Dermoscopy of a skin lesion.
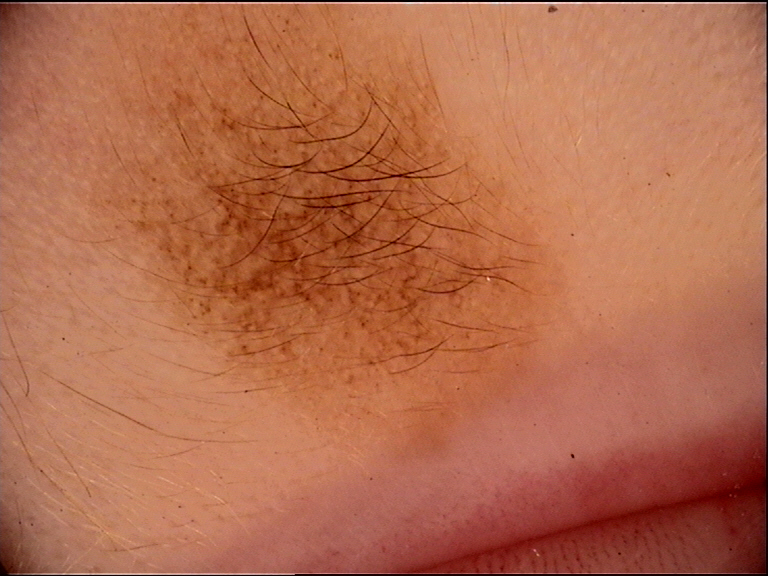category=banal; assessment=congenital compound nevus (expert consensus).